Recorded as skin type II. The chart notes alcohol use, prior malignancy (patient or family), pesticide exposure, prior skin cancer (patient or family), and no tobacco use. A female subject in their mid-50s:
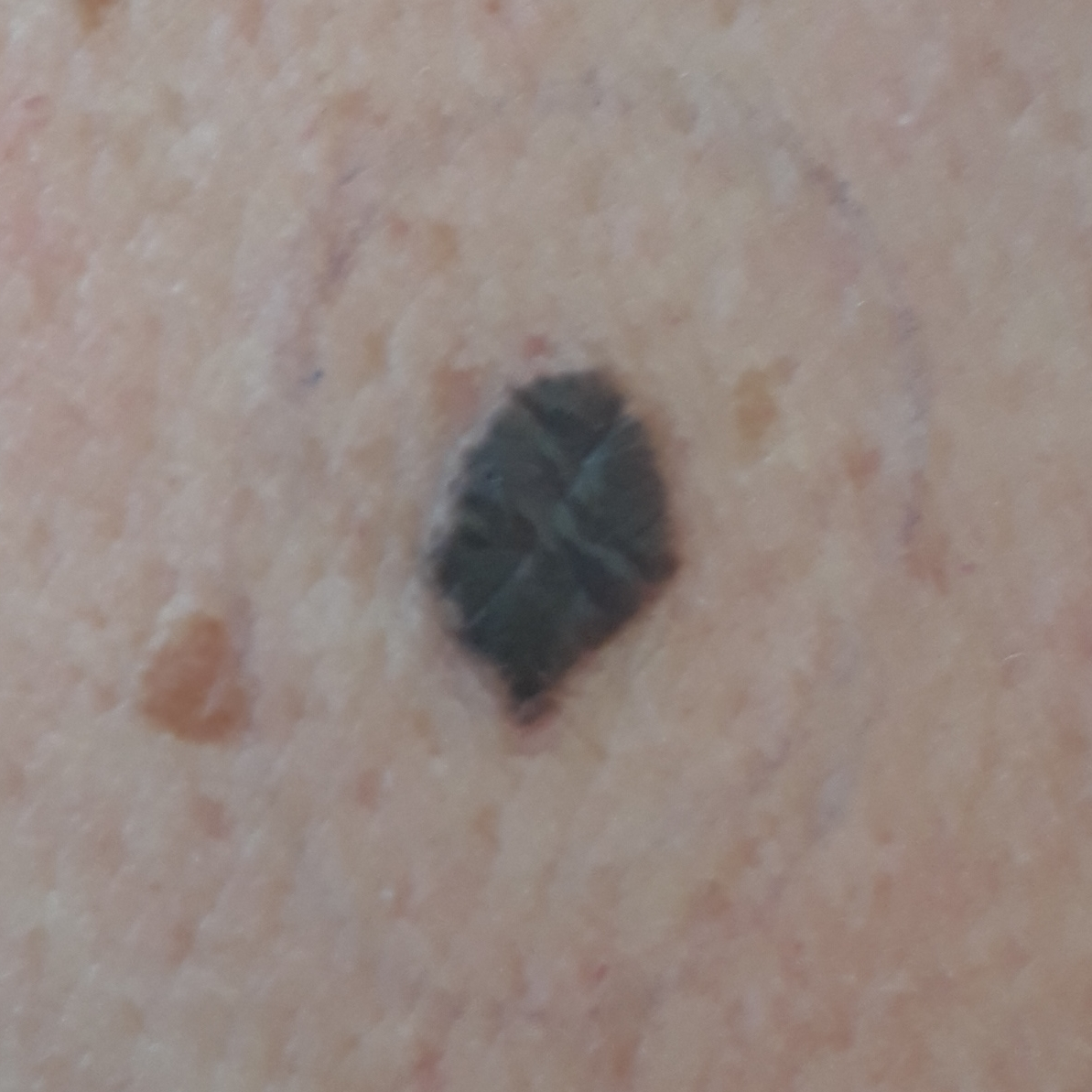Summary: Asymptomatic by report. Conclusion: Histopathology confirmed a melanoma.